Dermoscopy of a skin lesion.
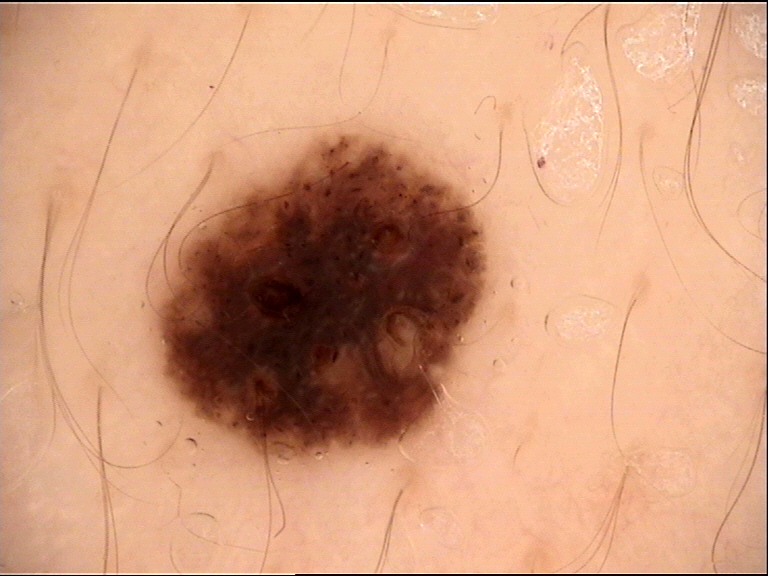Labeled as a benign lesion — a dysplastic compound nevus.